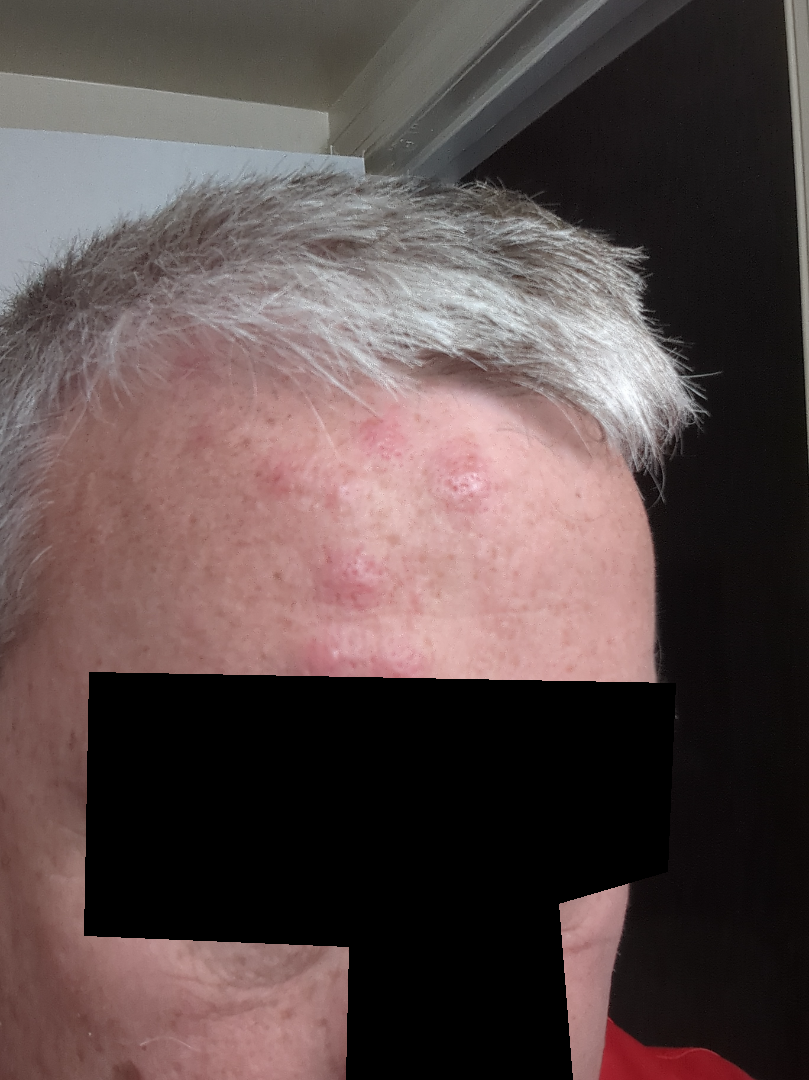assessment: not assessable
patient's own categorization: a rash
photo taken: close-up
systemic symptoms: none reported
patient: male, age 50–59
skin tone: Fitzpatrick phototype II; non-clinician graders estimated MST 2 or 3
duration: less than one week
lesion texture: raised or bumpy
body site: head or neck